The leg is involved · the photo was captured at a distance · female contributor, age 70–79.
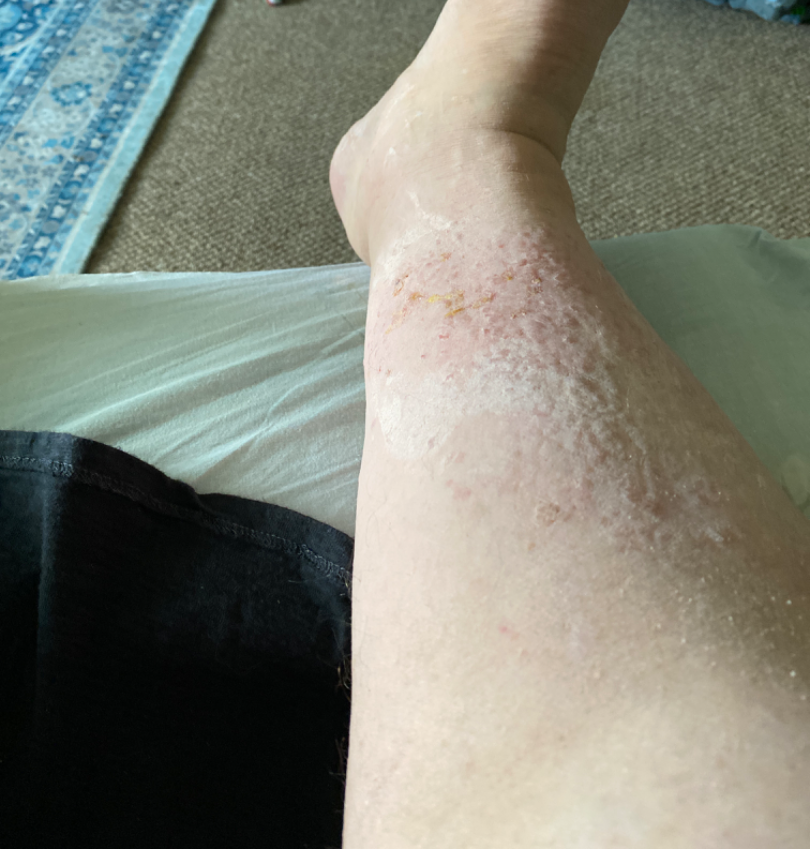reported symptoms=itching
other reported symptoms=none reported
lesion texture=raised or bumpy
present for=less than one week
clinical impression=the leading consideration is Stasis Dermatitis; also raised was Pretibial myxedema; lower on the differential is Amyloidosis of skin